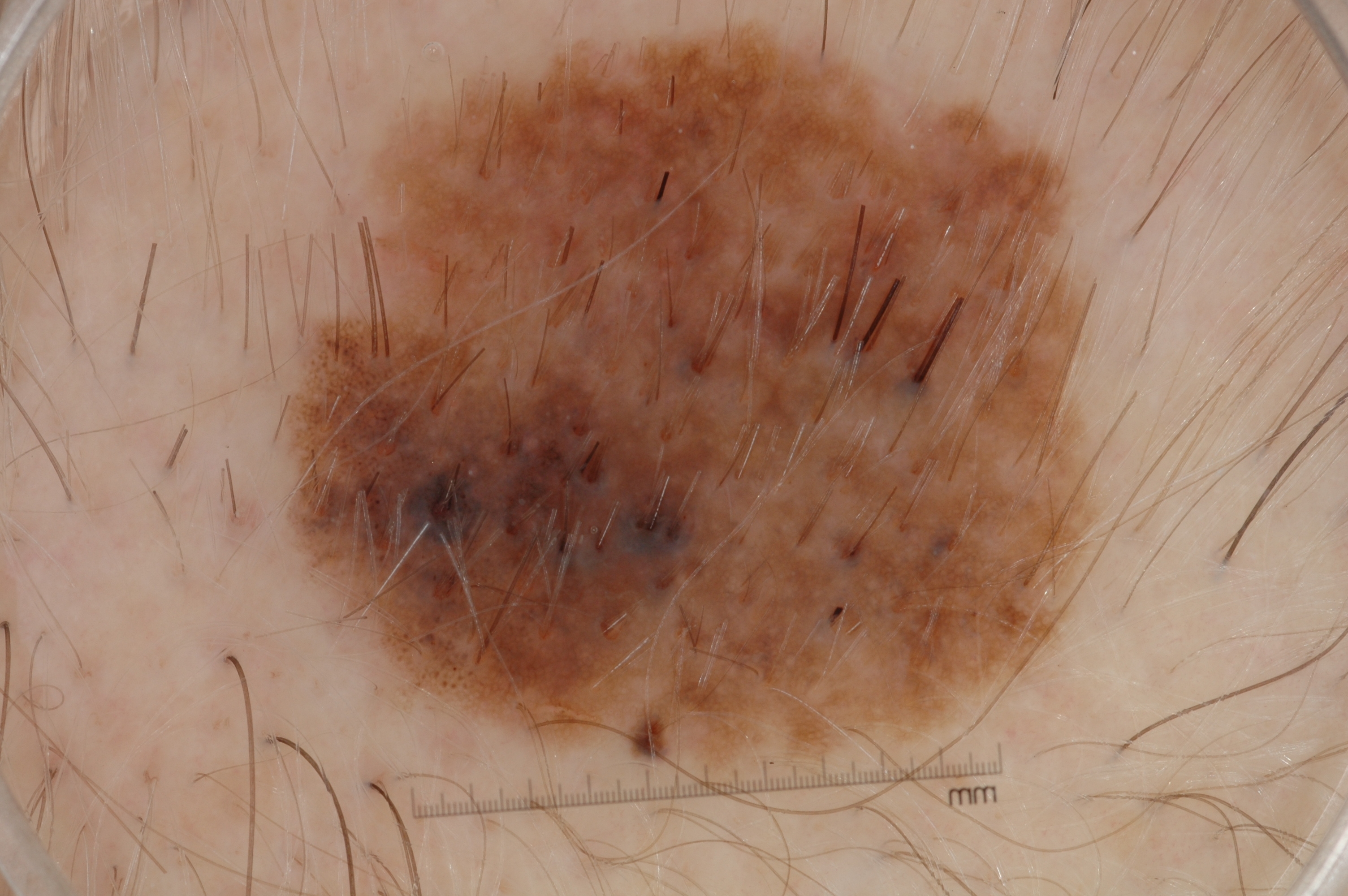| key | value |
|---|---|
| modality | dermoscopic image |
| subject | male, roughly 60 years of age |
| features | pigment network and milia-like cysts |
| lesion bbox | left=285, top=28, right=1095, bottom=770 |
| impression | a melanoma |